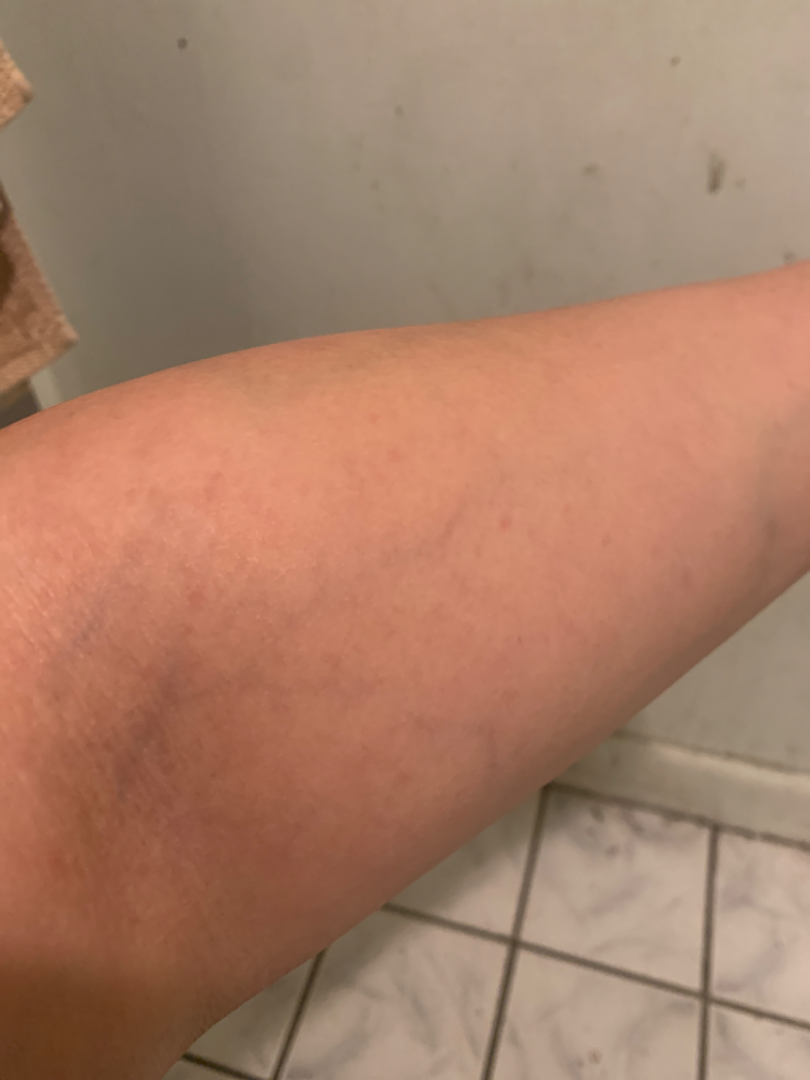The affected area is the arm.
The contributor is a female aged 30–39.
This image was taken at an angle.
Three independent reviewers: the favored diagnosis is Insect Bite; also raised was Eczema; also consider Molluscum Contagiosum.